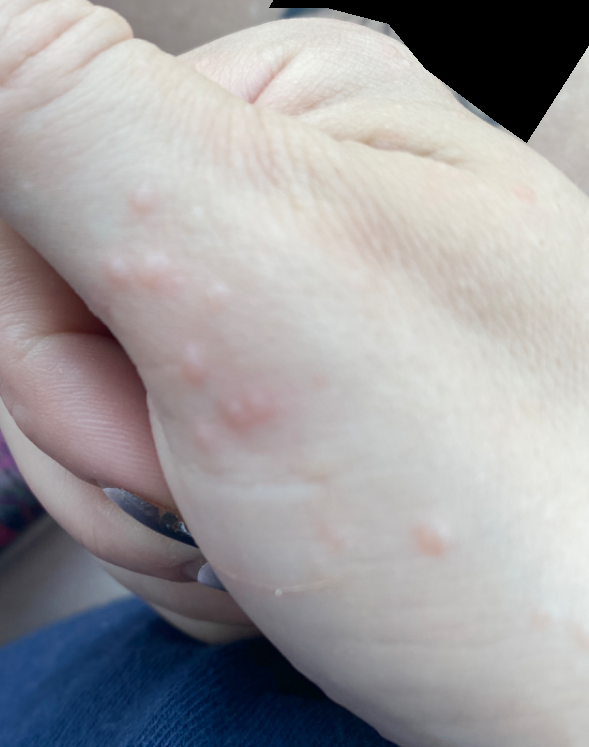A close-up photograph. The affected area is the palm. The patient is a female aged 18–29. On remote dermatologist review, Verruca vulgaris (weight 0.41); Molluscum Contagiosum (weight 0.41); Acrokeratosis verruciformis (weight 0.18).